This is a close-up image; skin tone: Fitzpatrick skin type II — 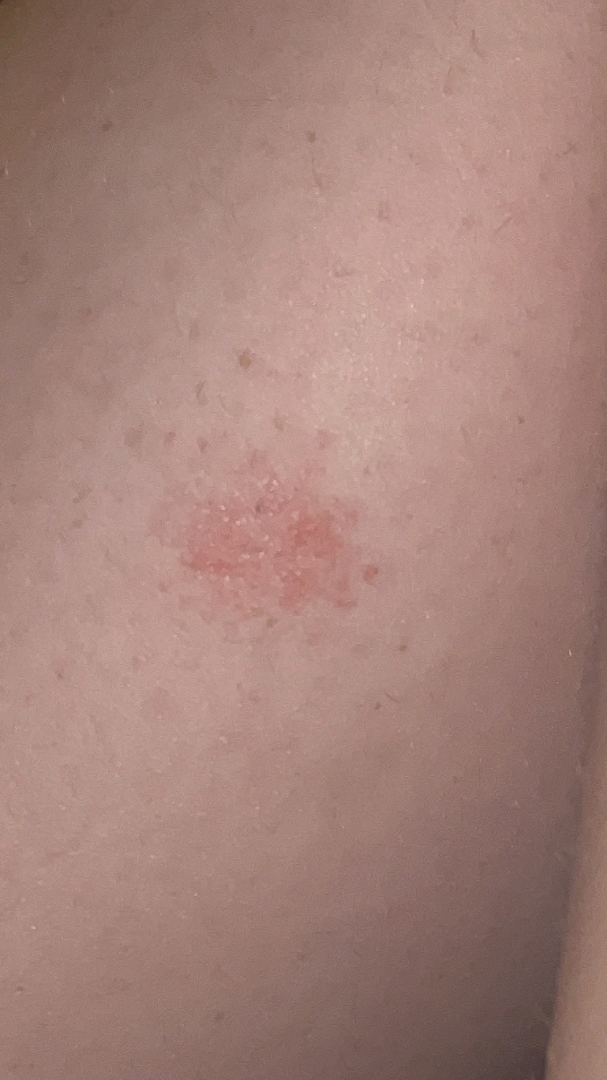A single dermatologist reviewed the case: the leading impression is Eczema; also consider Insect Bite.